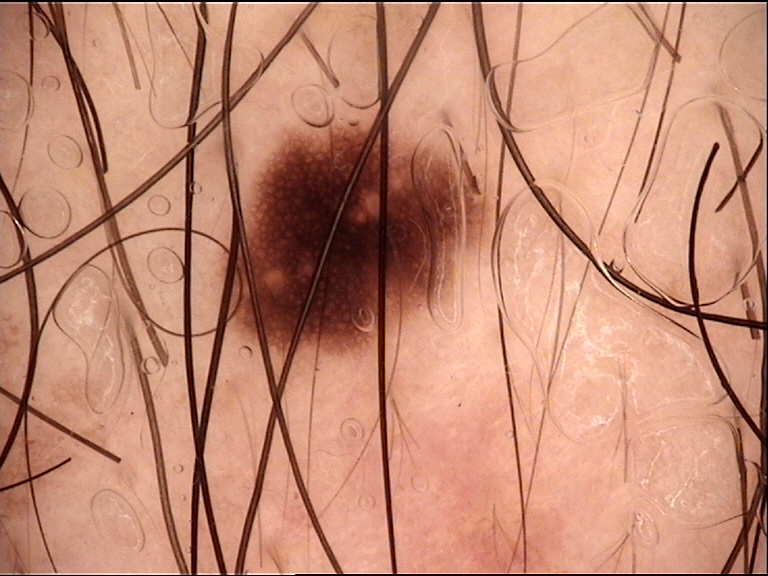The diagnostic label was a dysplastic junctional nevus.